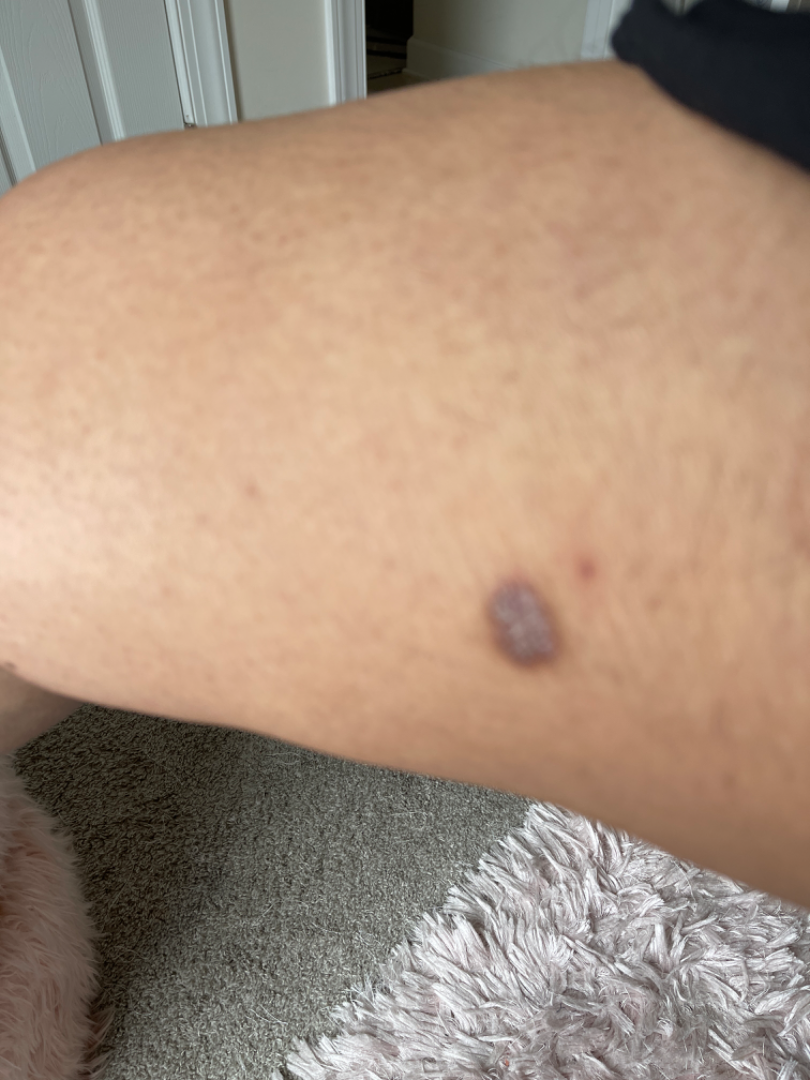The patient considered this a rash. Symptoms reported: bothersome appearance. Reported duration is three to twelve months. No associated systemic symptoms reported. Texture is reported as rough or flaky. Skin tone: FST III. This is a close-up image. Dermatofibroma and SK/ISK were considered with similar weight; a more distant consideration is Melanoma.